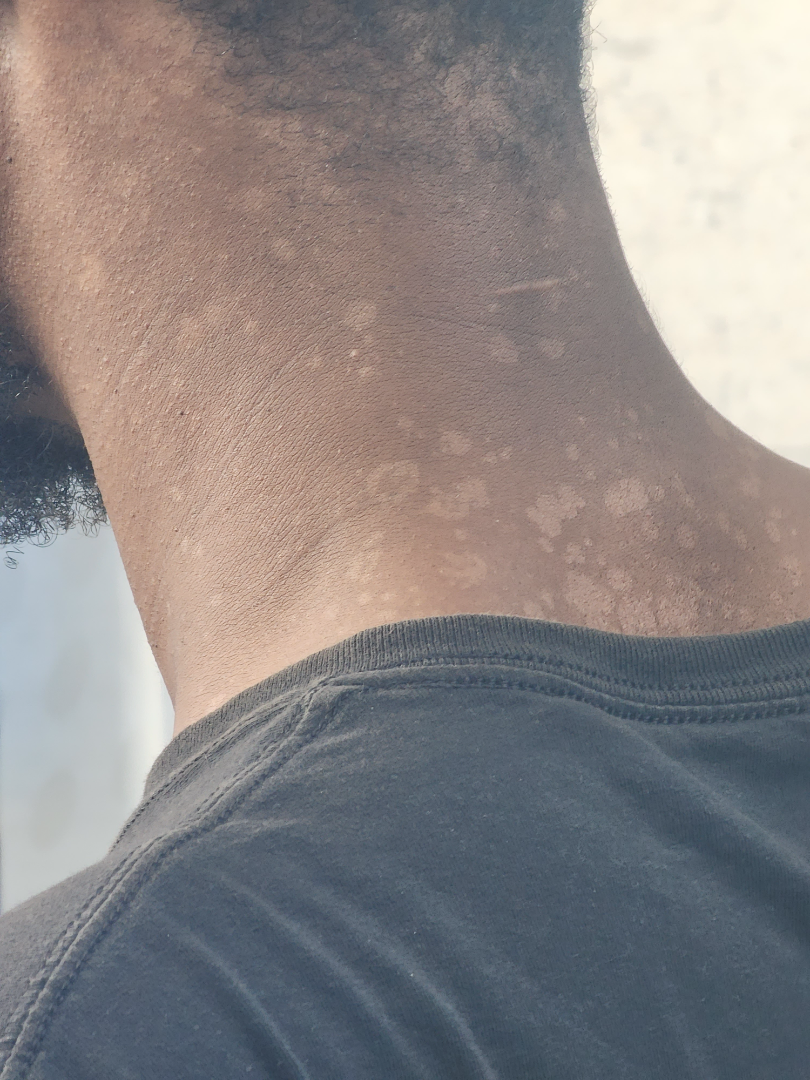<case>
  <body_site>arm, head or neck, back of the torso, front of the torso</body_site>
  <skin_tone>
    <fitzpatrick>VI</fitzpatrick>
    <monk_skin_tone>5, 8</monk_skin_tone>
  </skin_tone>
  <symptoms>enlargement, bothersome appearance</symptoms>
  <shot_type>close-up</shot_type>
  <differential>
    <leading>Tinea Versicolor</leading>
  </differential>
</case>